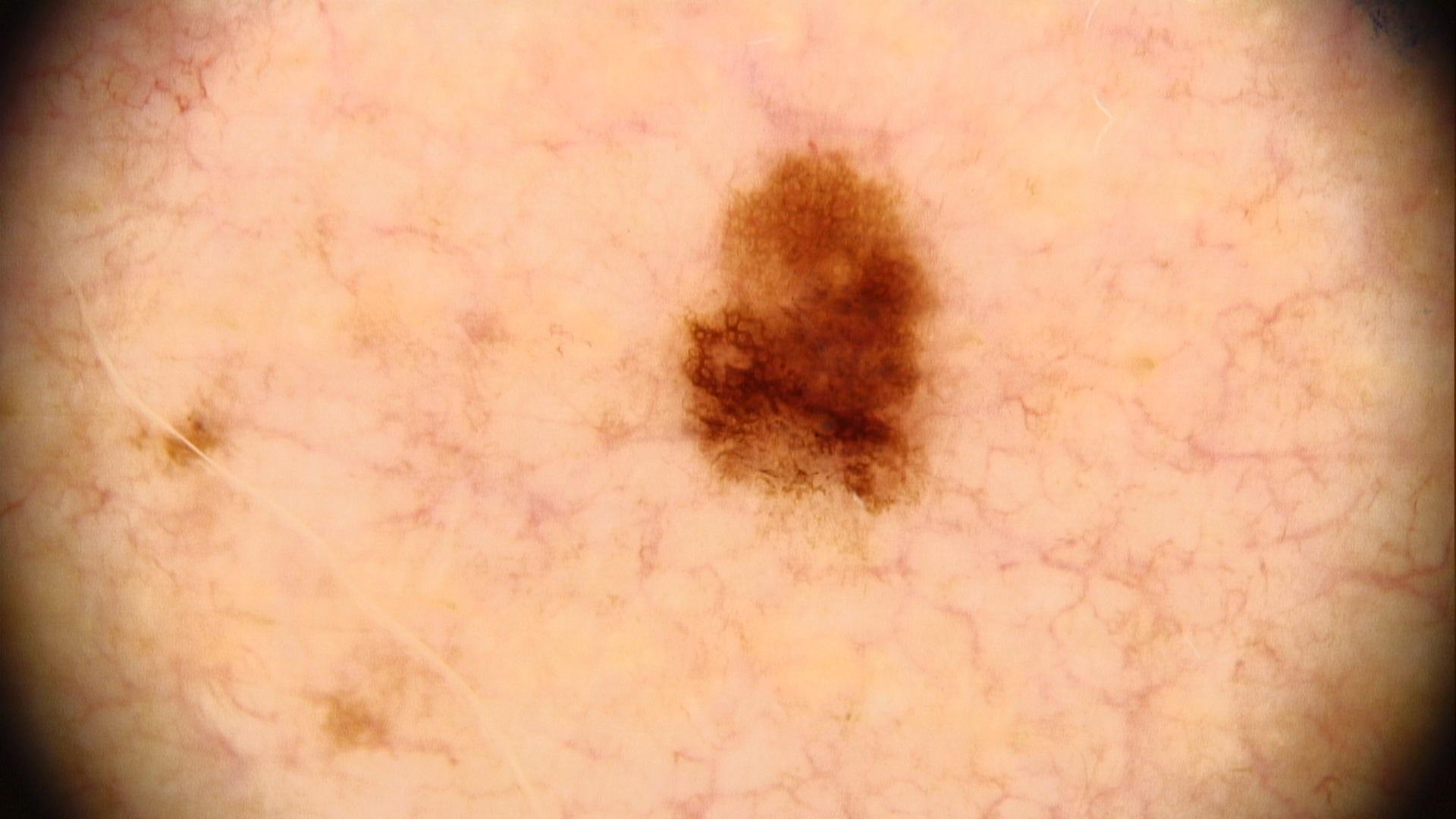Q: What are the patient's age and sex?
A: male, aged 43-47
Q: What is the imaging modality?
A: contact-polarized dermoscopy
Q: What did the workup show?
A: Nevus (biopsy-proven)